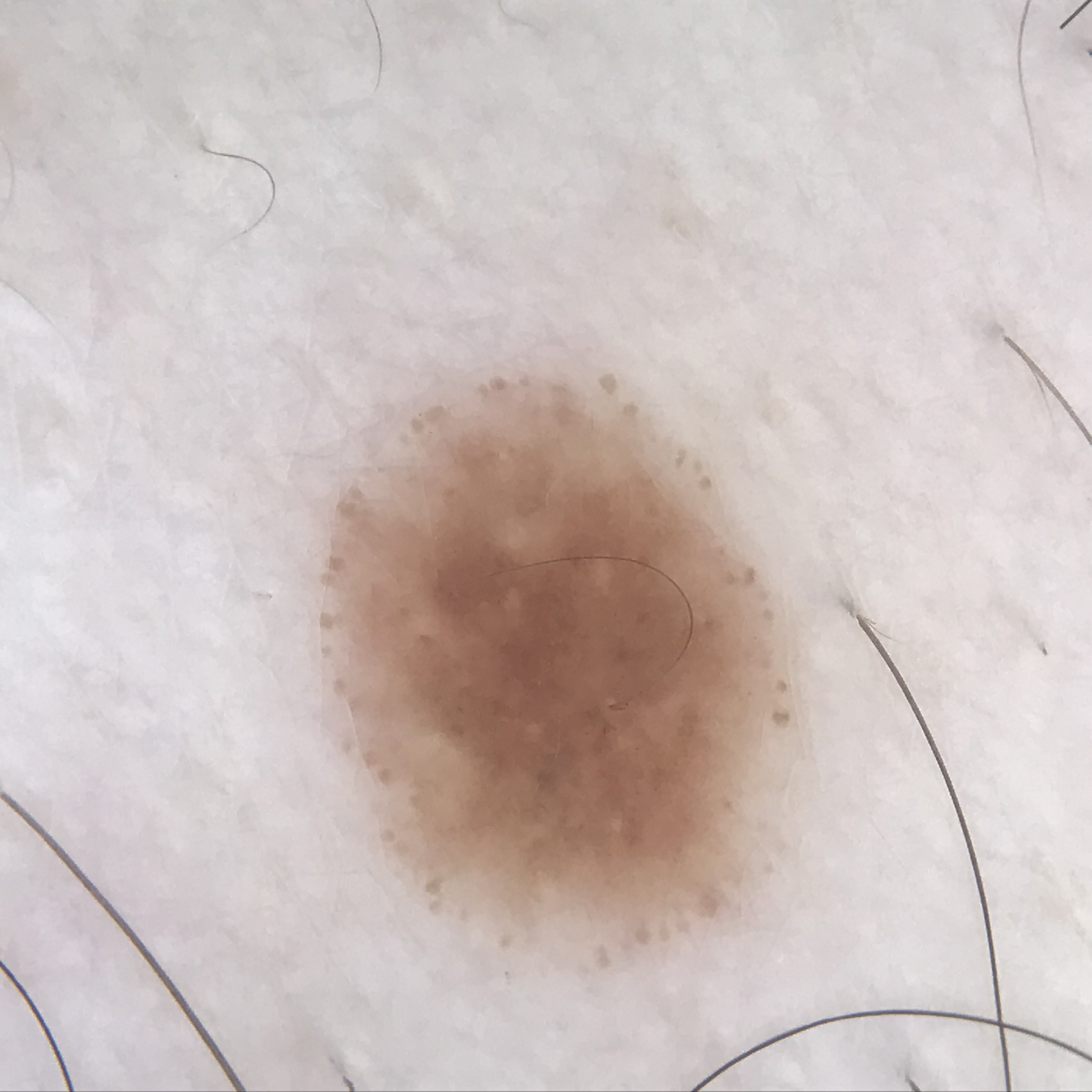A dermoscopic image of a skin lesion. Diagnosed as a dysplastic junctional nevus.